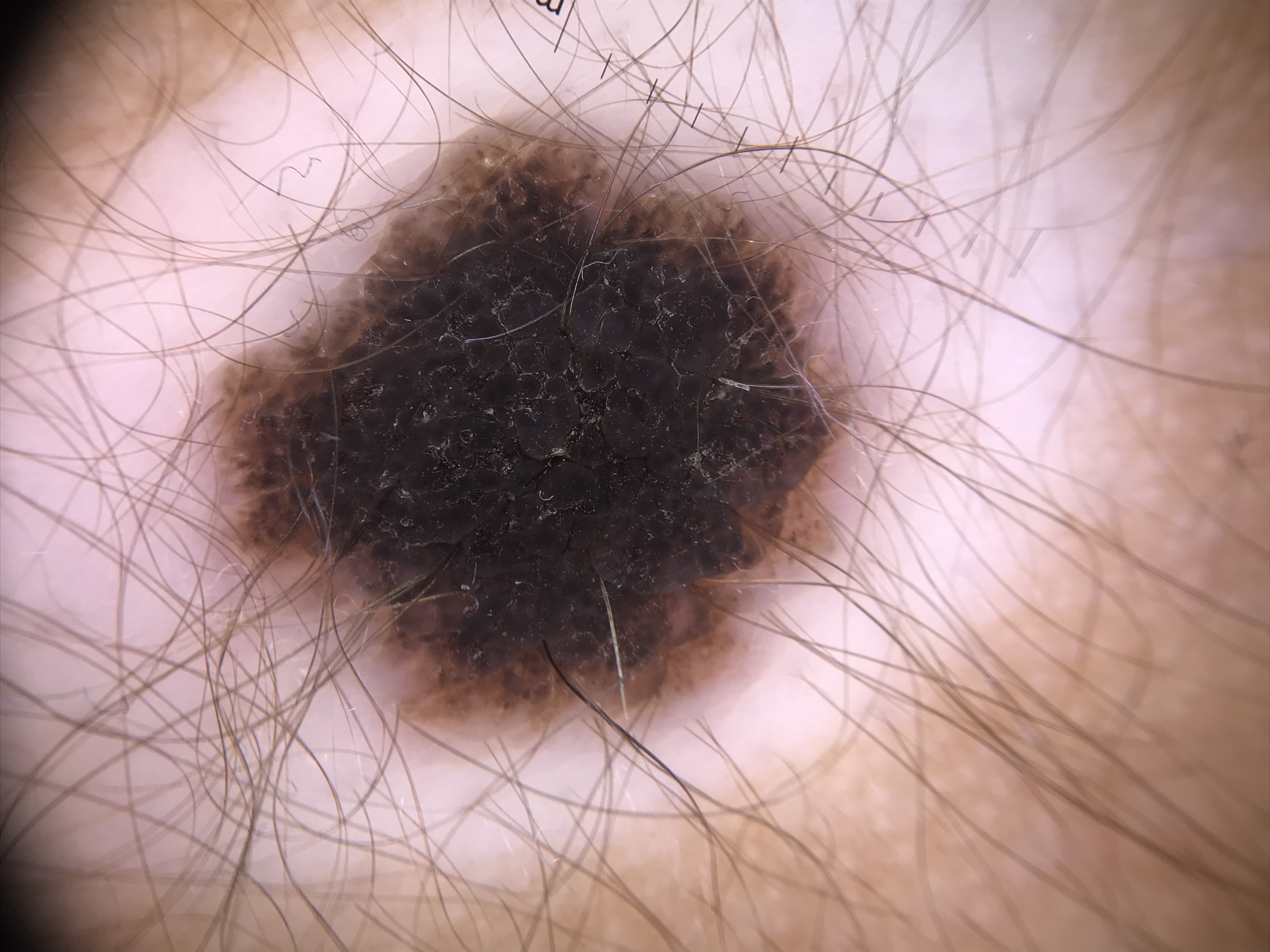A dermoscopy image of a single skin lesion. Classified as a banal lesion — a congenital compound nevus.